This image was taken at a distance. The affected area is the leg. The contributor is 40–49, female:
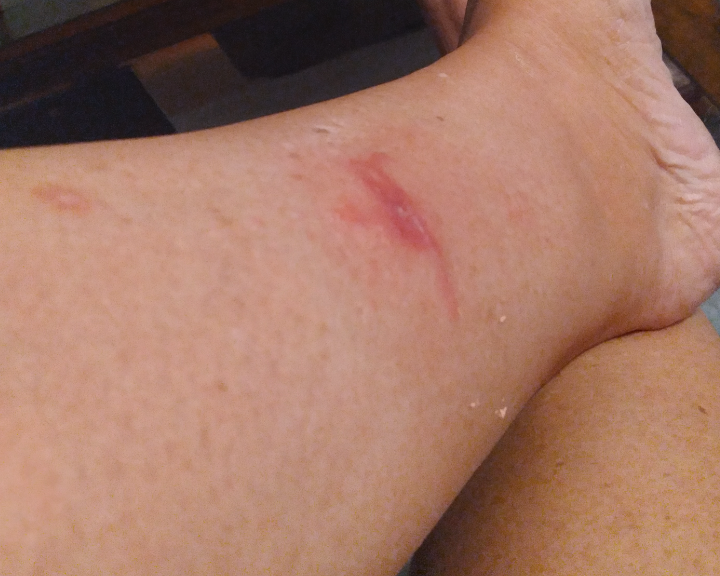{"assessment": "unable to determine"}